The affected area is the arm. The contributor is female. This image was taken at an angle.
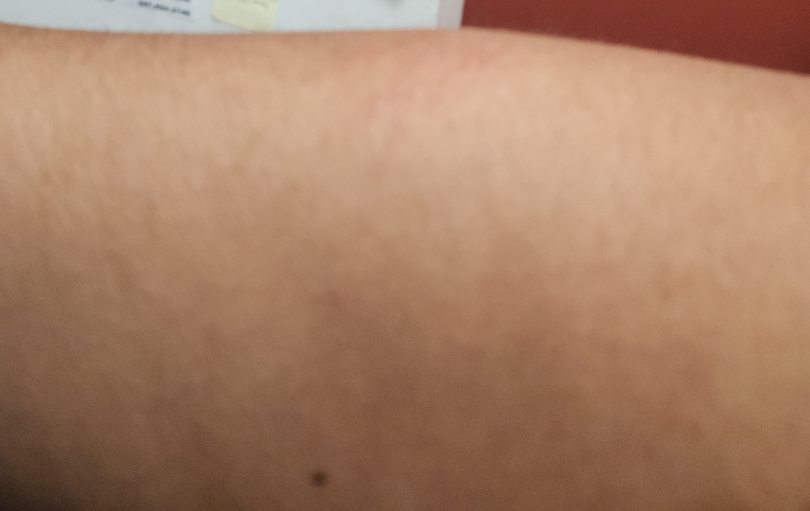The contributor reports the lesion is raised or bumpy and rough or flaky. Skin tone: human graders estimated Monk skin tone scale 6 (US pool) or 4 (India pool). Reported duration is one to four weeks. Eczema (leading); Contact dermatitis (considered); Tinea (lower probability).